The affected area is the arm, the photograph is a close-up of the affected area, the contributor is a female aged 70–79: 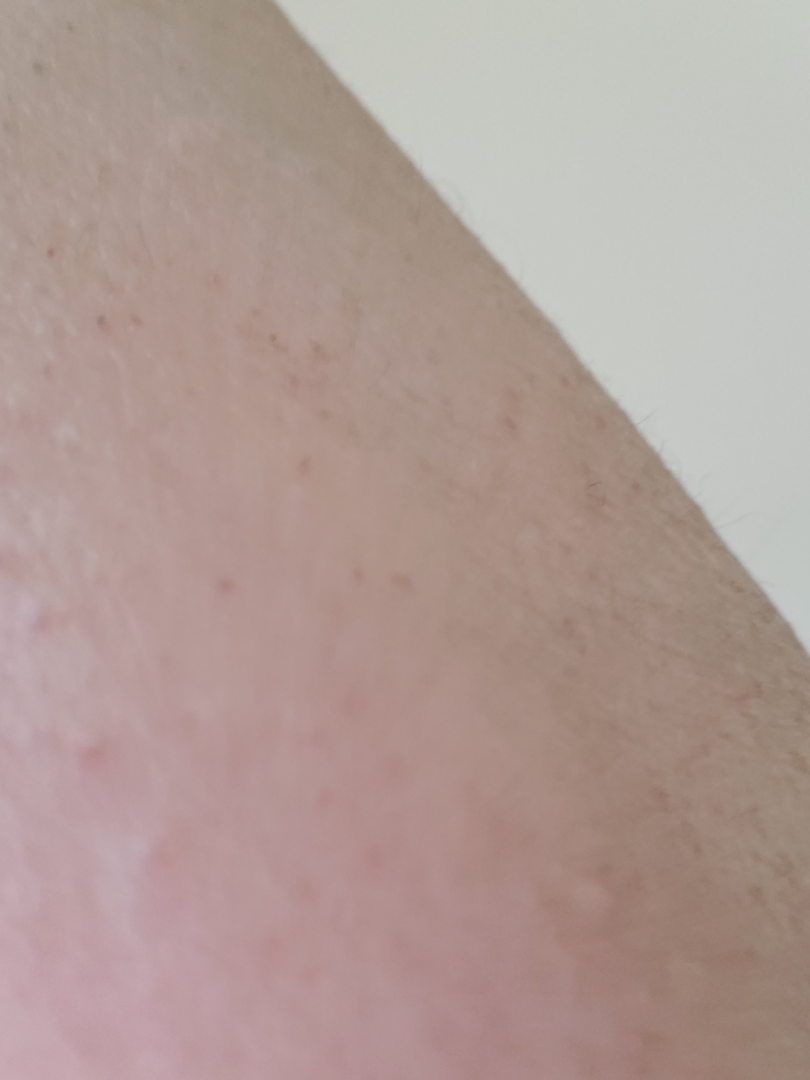{"assessment": "not assessable", "systemic_symptoms": "none reported", "patient_category": "a rash", "symptoms": "itching", "duration": "about one day", "texture": "raised or bumpy", "skin_tone": {"fitzpatrick": "III", "fitzpatrick_source": "self_reported", "monk_skin_tone": [1, 2]}}